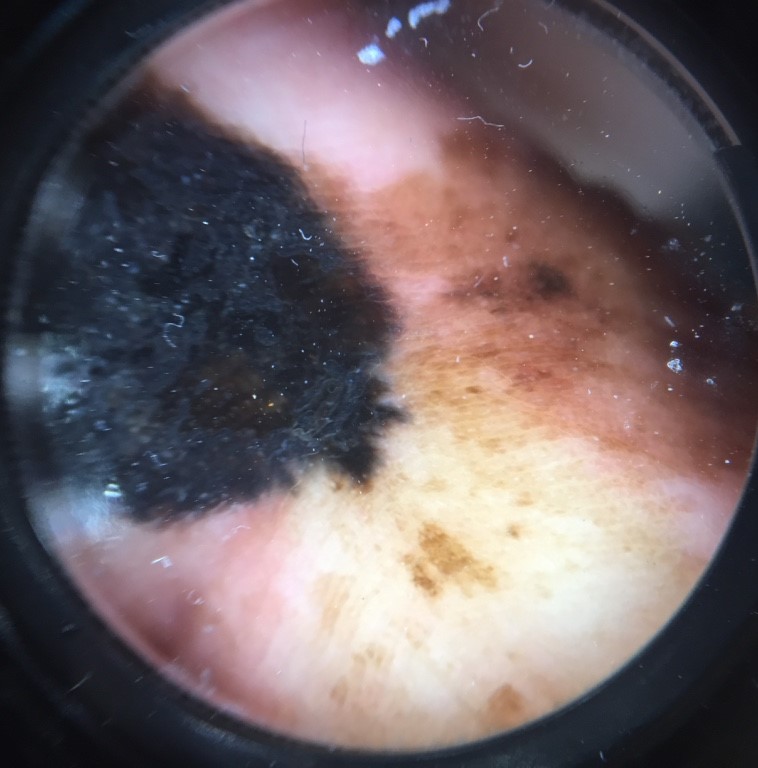A dermoscopic photograph of a skin lesion.
The biopsy diagnosis was an acral lentiginous melanoma.